A dermoscopic photograph of a skin lesion.
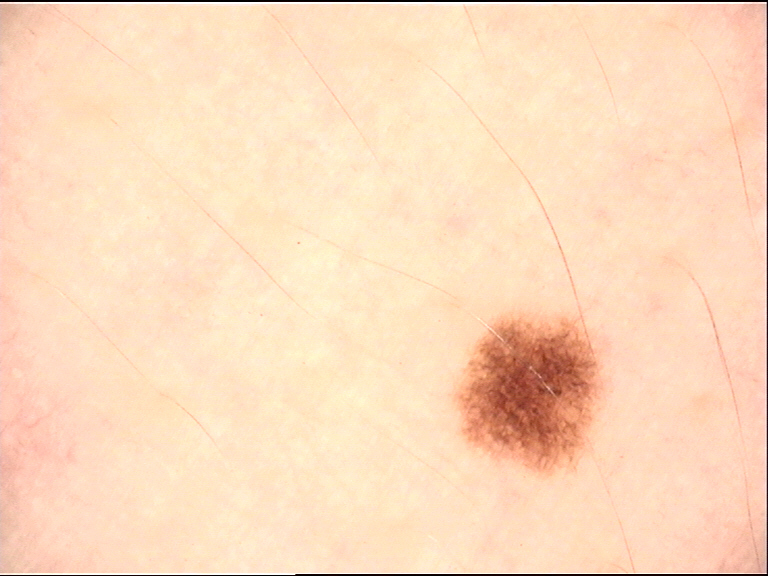Classified as a banal lesion — a junctional nevus.